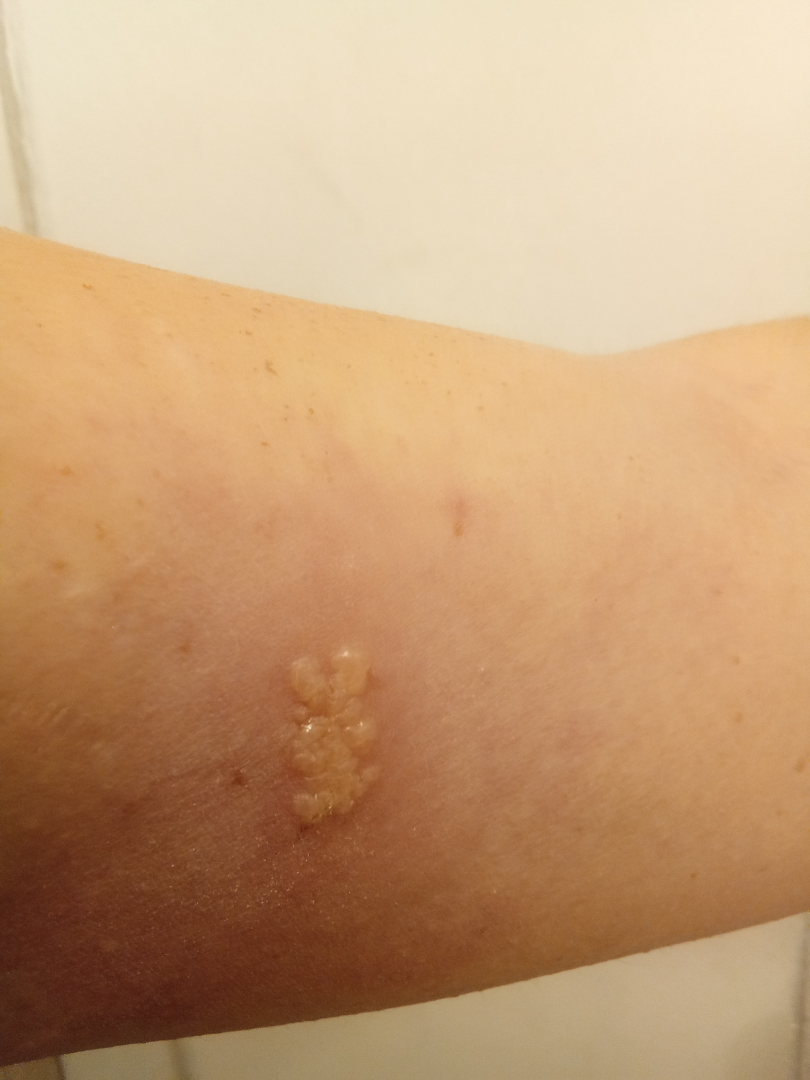Q: How does the patient describe it?
A: a rash
Q: Image view?
A: close-up
Q: Anatomic location?
A: arm
Q: Texture?
A: fluid-filled
Q: Duration?
A: more than one year
Q: What is the patient's skin tone?
A: Fitzpatrick phototype III
Q: Constitutional symptoms?
A: none reported
Q: Age and sex?
A: female, age 18–29
Q: What conditions are considered?
A: single-reviewer assessment: Herpes Zoster and Herpes Simplex were considered with similar weight; a more distant consideration is Allergic Contact Dermatitis